A dermoscopic image of a skin lesion.
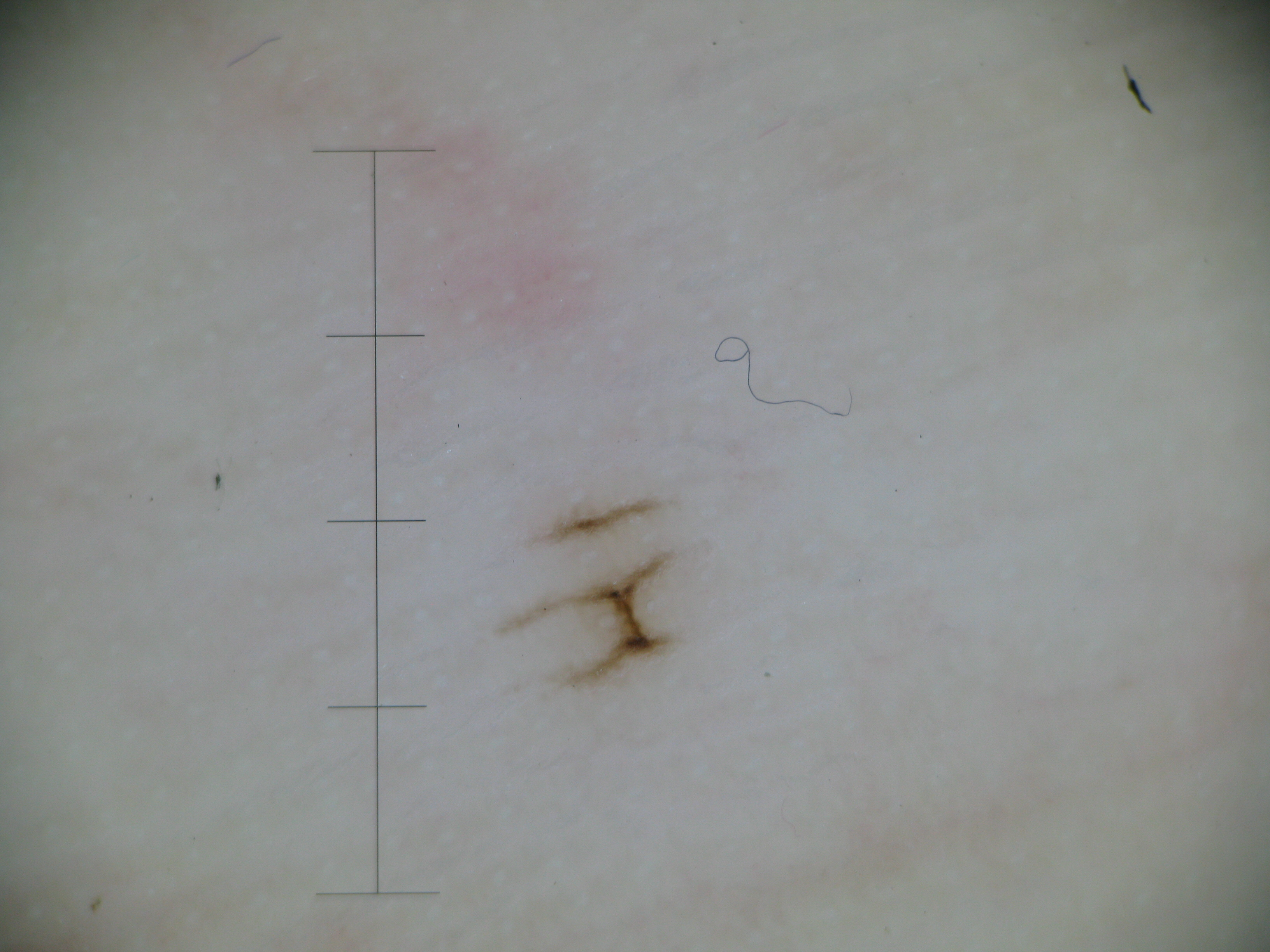Consistent with a banal lesion — an acral junctional nevus.